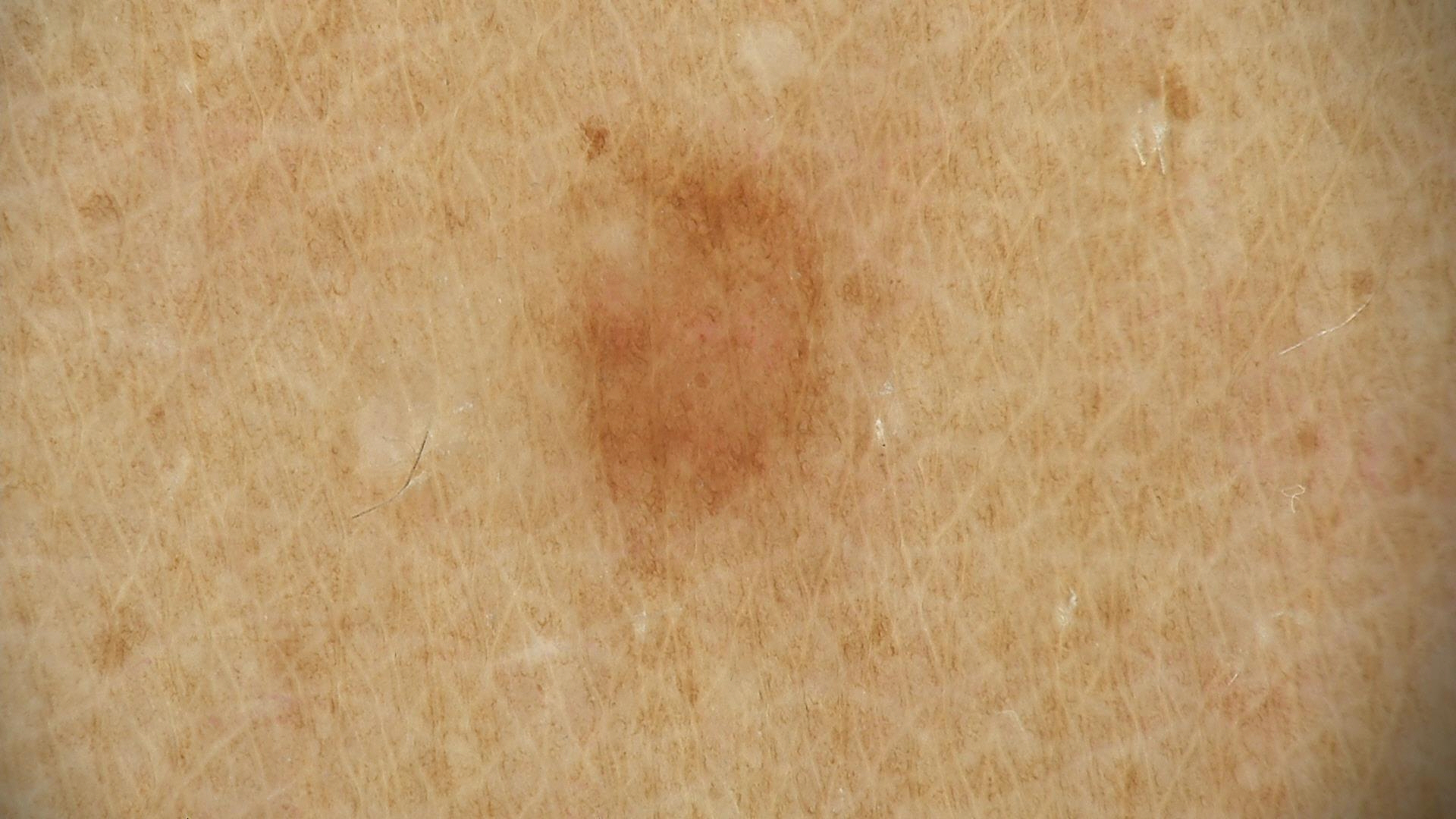modality = dermatoscopy, assessment = dysplastic junctional nevus (expert consensus).